A dermoscopic close-up of a skin lesion:
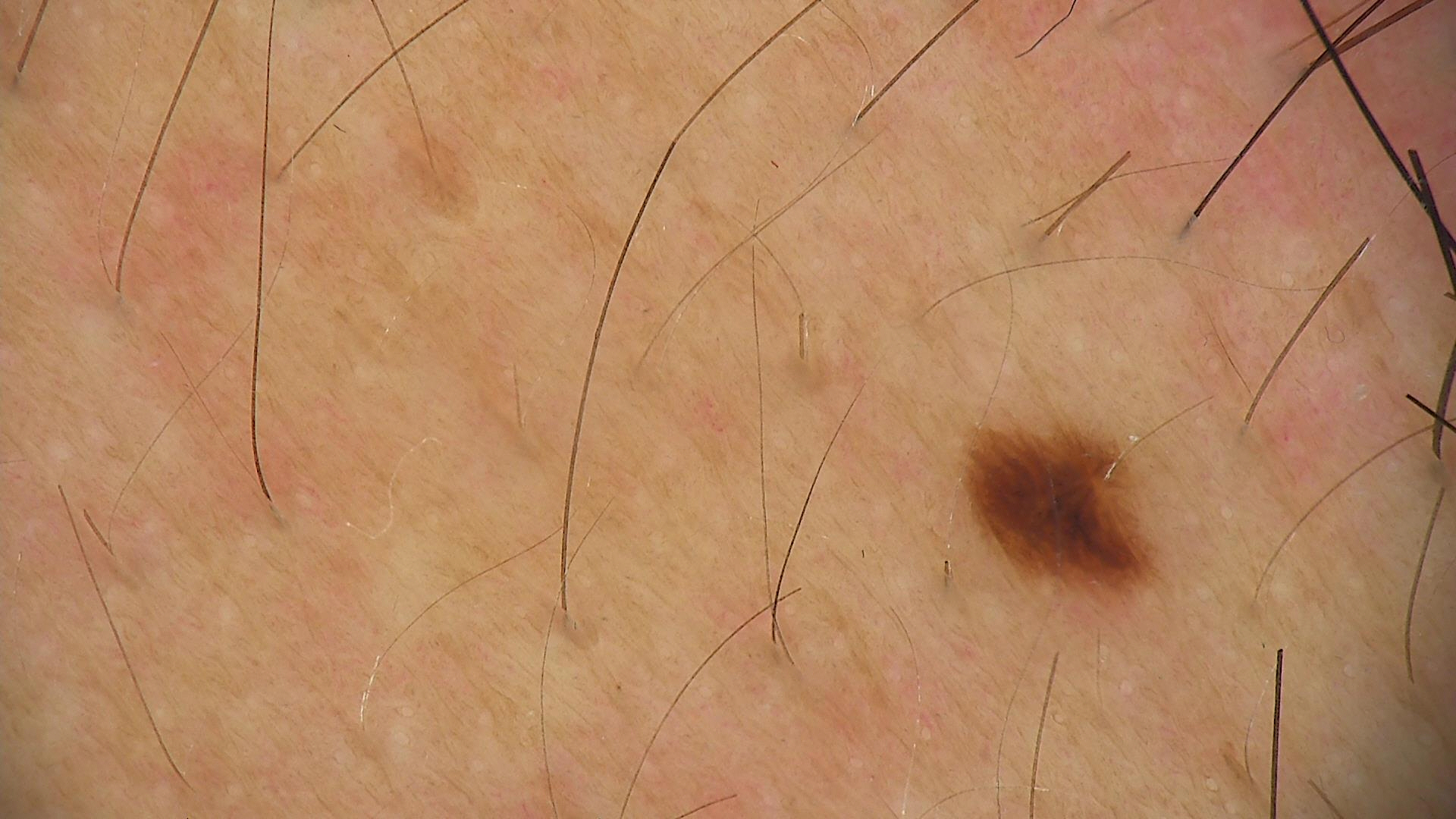The diagnostic label was a benign lesion — a dysplastic junctional nevus.